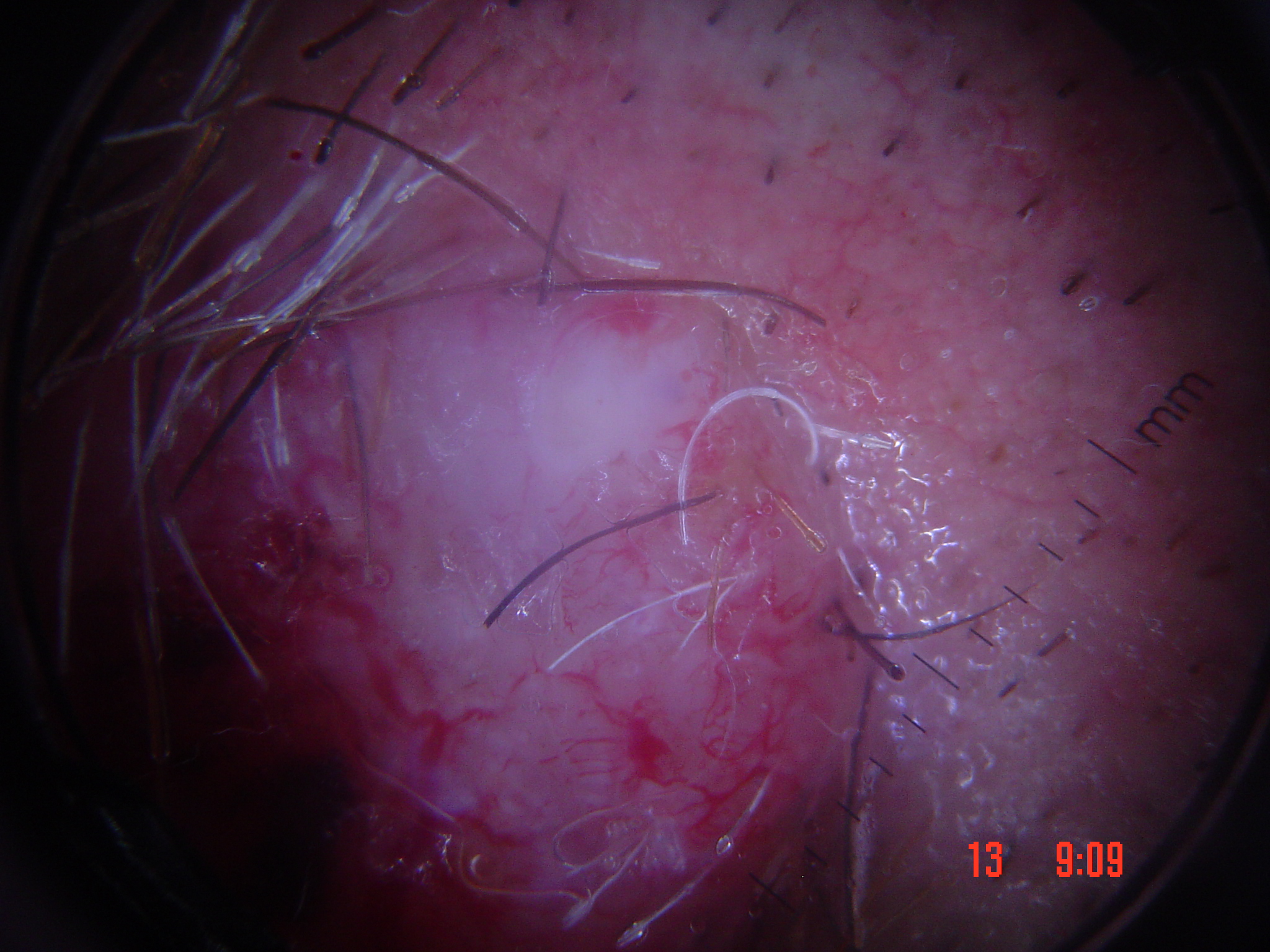A dermoscopic photograph of a skin lesion. Histopathology confirmed a keratinocytic lesion — a squamous cell carcinoma.